Reported duration is less than one week. Close-up view. The patient considered this acne. No constitutional symptoms were reported. Texture is reported as raised or bumpy. Skin tone: Fitzpatrick phototype IV; lay reviewers estimated Monk Skin Tone 2–3. Located on the leg. Male subject, age 30–39. No associated lesion symptoms were reported — 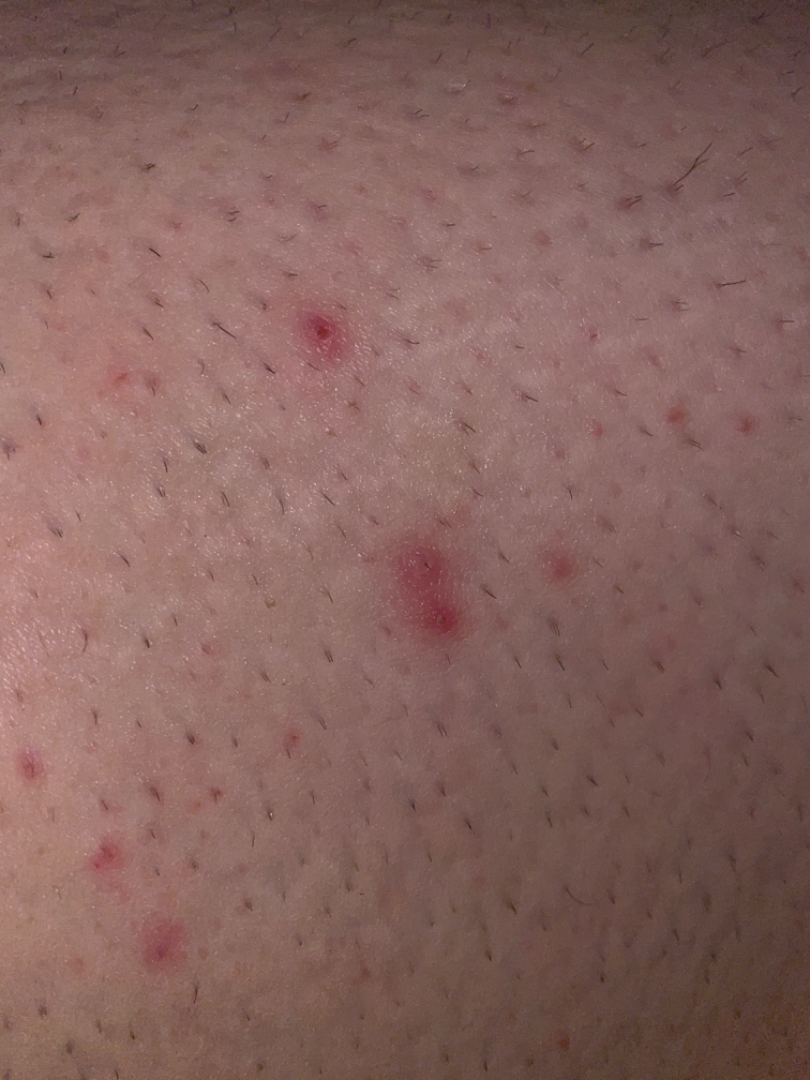assessment: the impression is Folliculitis.